A dermatoscopic image of a skin lesion.
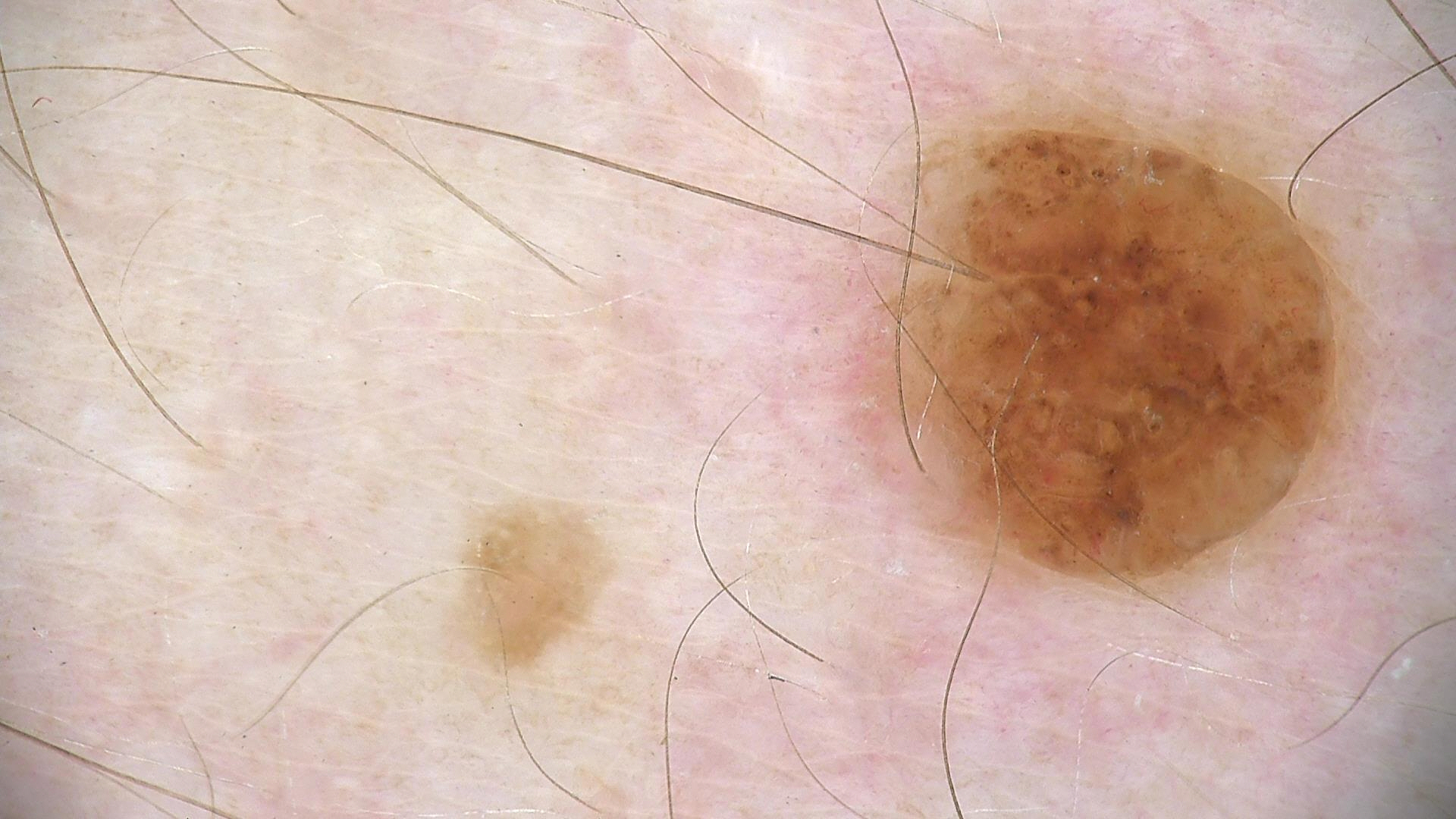The diagnosis was a banal lesion — a dermal nevus.